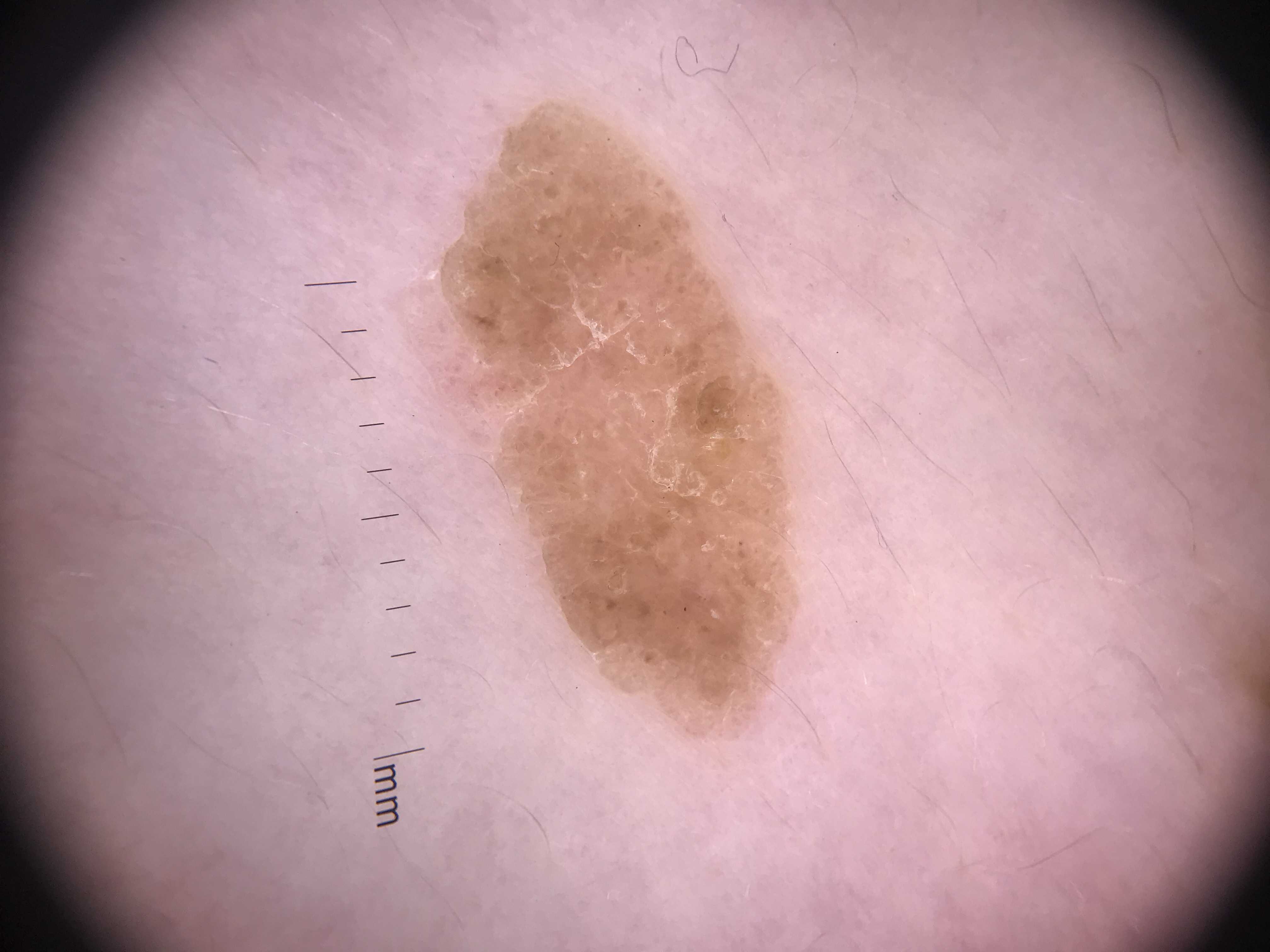image — dermoscopy
subtype — keratinocytic
diagnosis — seborrheic keratosis (expert consensus)